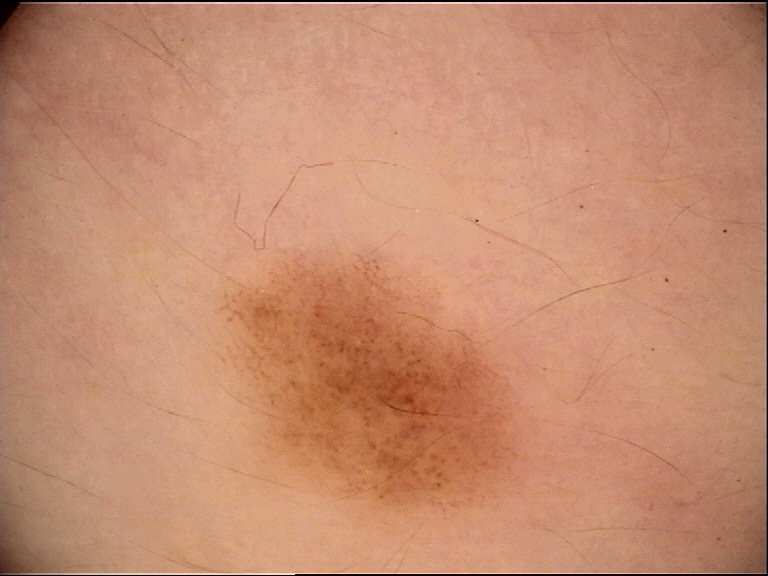Case:
A skin lesion imaged with a dermatoscope.
Impression:
Diagnosed as a benign lesion — a dysplastic junctional nevus.